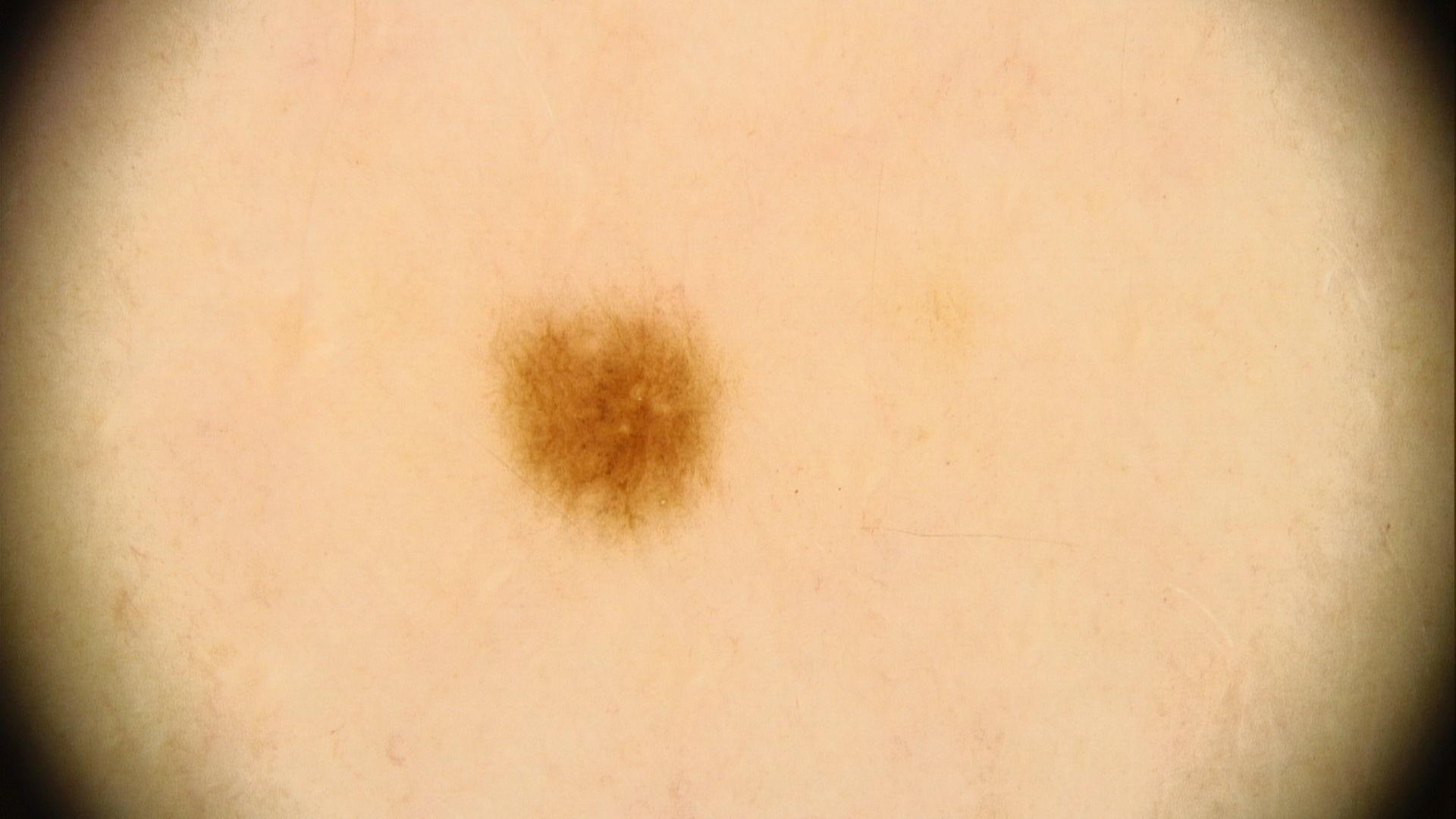Notes:
– skin type — III
– relevant background — melanoma in a first-degree relative
– imaging — dermatoscopic image
– anatomic site — the trunk
– impression — Nevus